The patient is 50–59, female; close-up view; the lesion involves the leg and arm:
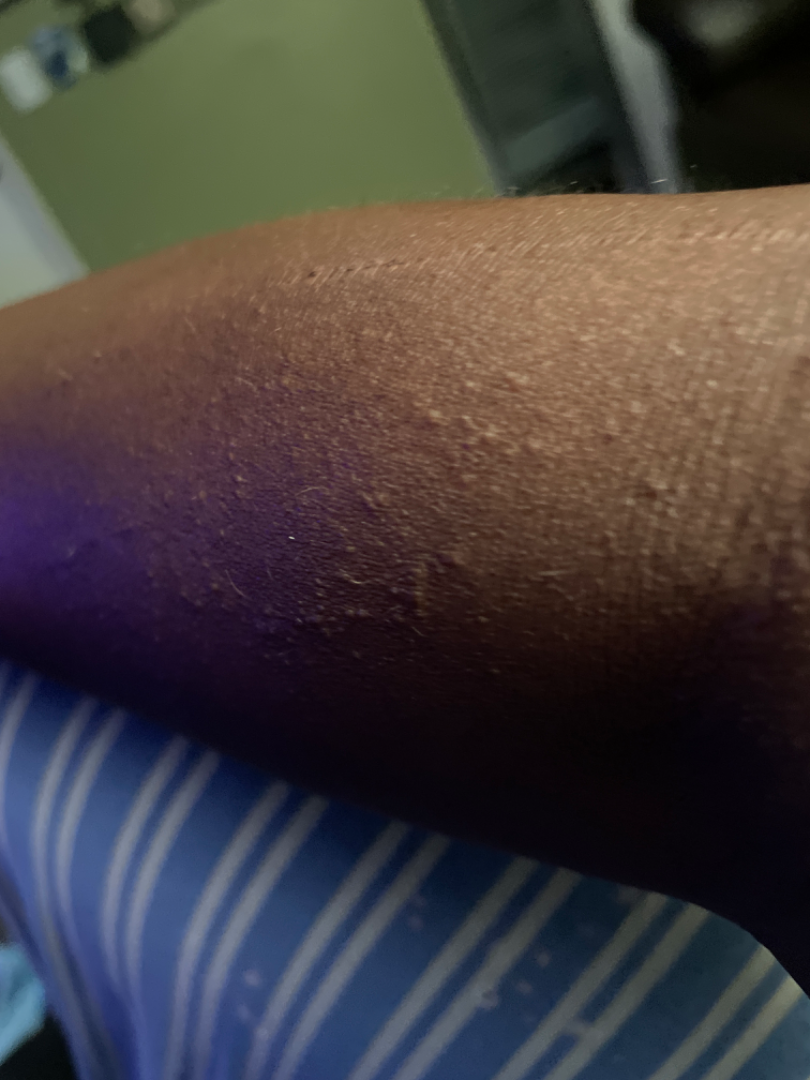On remote dermatologist review: the impression on review was Eczema.